A dermatoscopic image of a skin lesion:
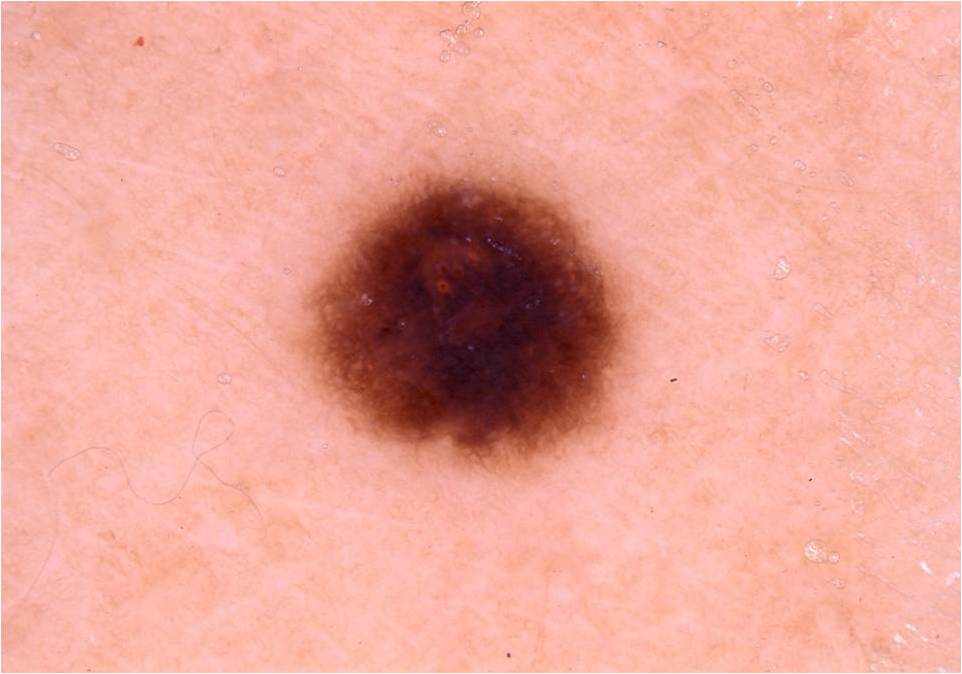The dermoscopic pattern shows pigment network; no globules, streaks, milia-like cysts, or negative network.
The lesion spans (289, 158, 649, 482).
The clinical diagnosis was a melanocytic nevus, a benign skin lesion.